The photograph was taken at a distance · the contributor is a female aged 18–29 · located on the leg and arm.
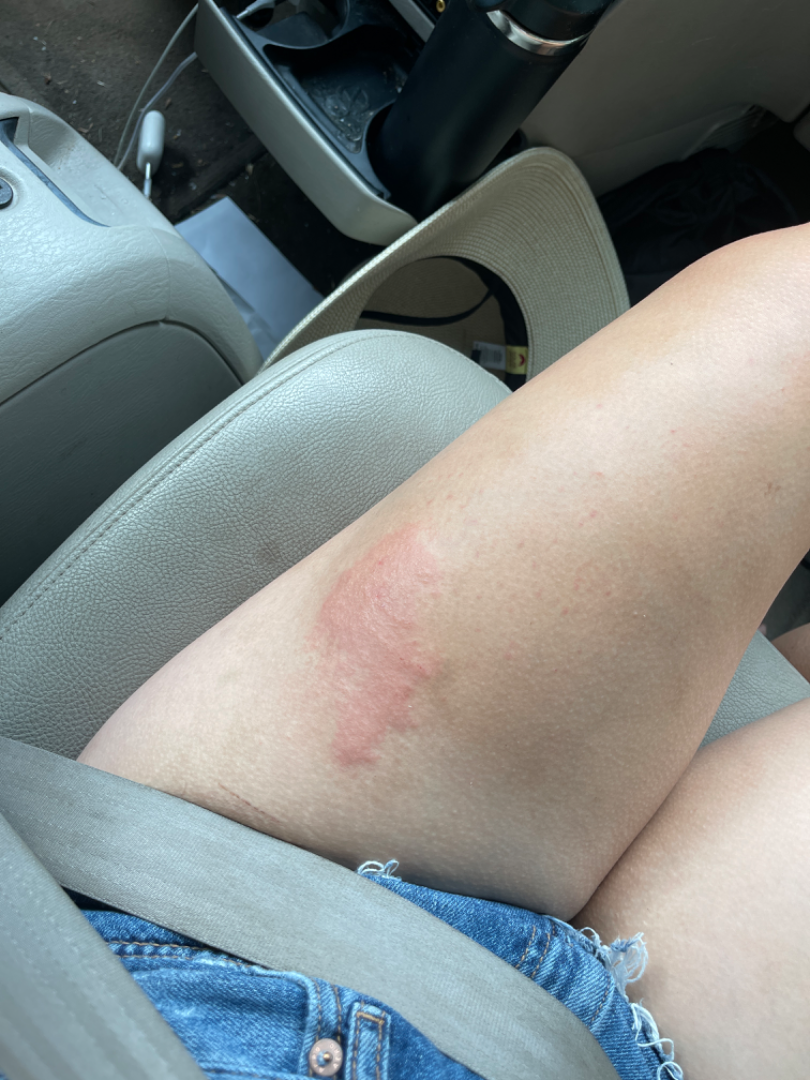{"assessment": "ungradable on photographic review"}